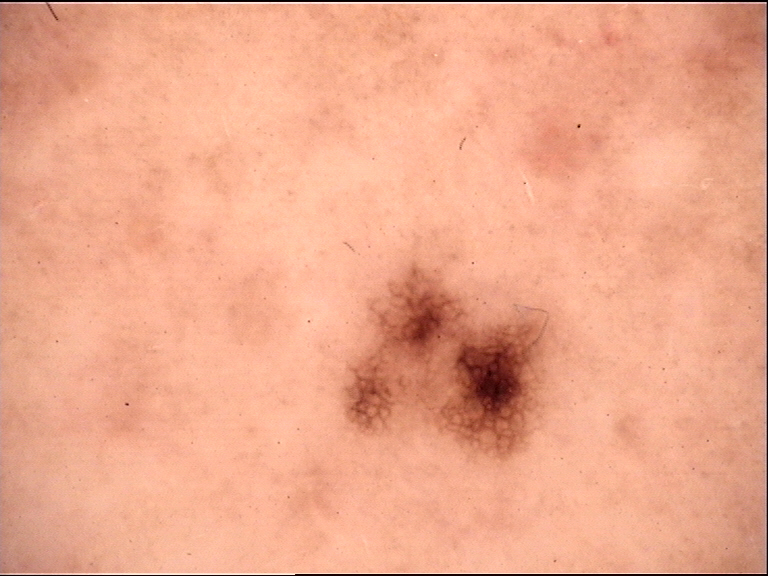Conclusion:
Diagnosed as a dysplastic junctional nevus.